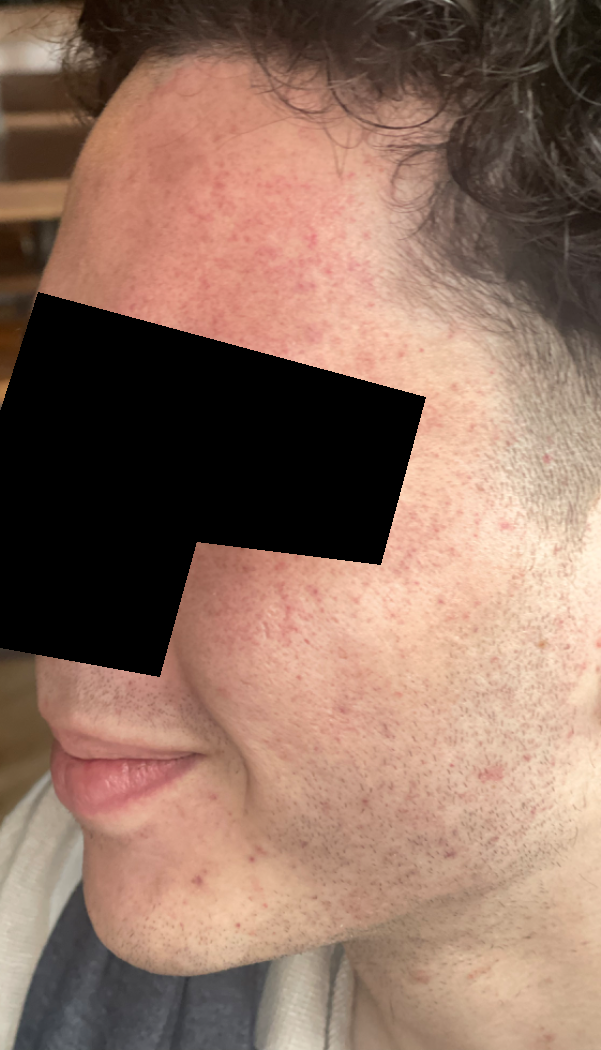History: The photograph is a close-up of the affected area. The lesion involves the head or neck. Impression: Most consistent with Rosacea.